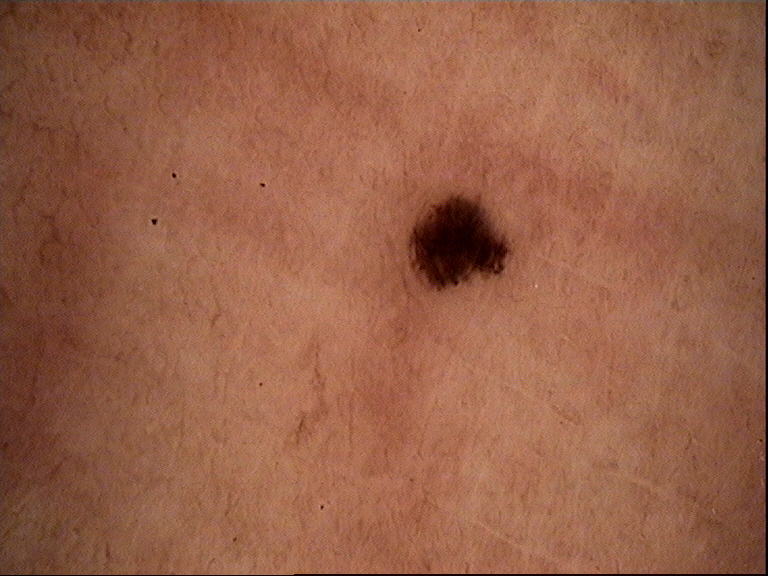{"image": "dermoscopy", "diagnosis": {"name": "dysplastic junctional nevus", "code": "jd", "malignancy": "benign", "super_class": "melanocytic", "confirmation": "expert consensus"}}